The patient is 18–29, female; the palm and back of the hand are involved; this image was taken at an angle: 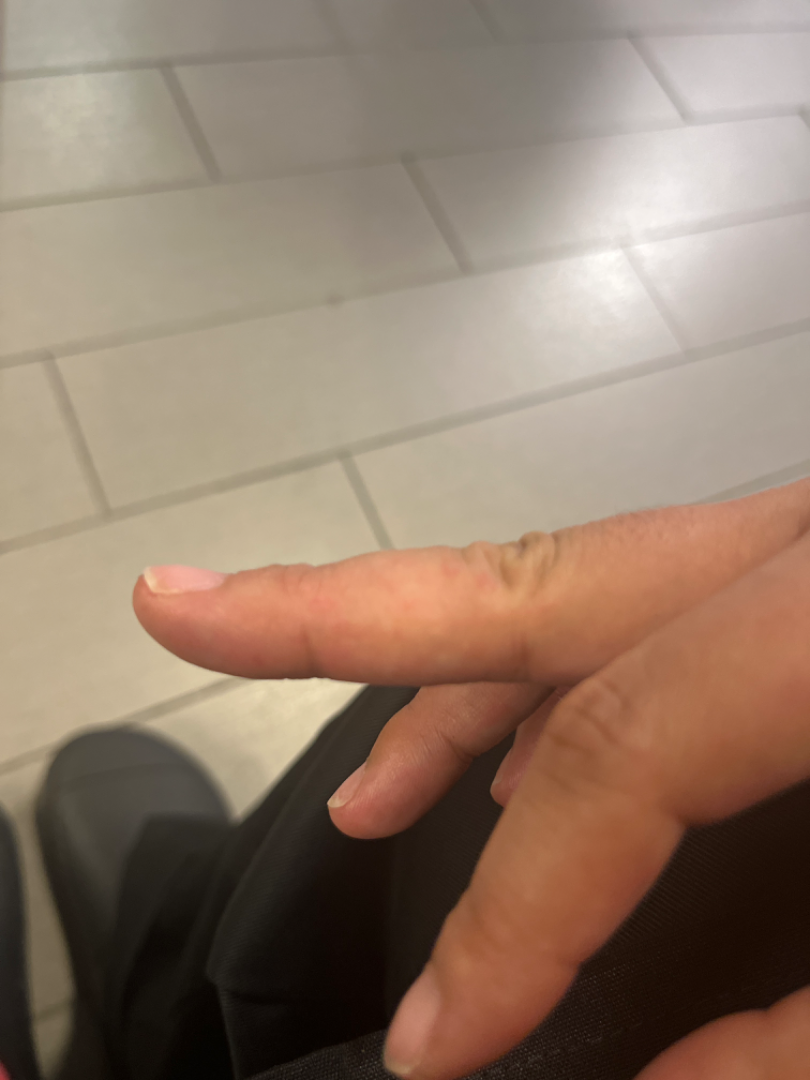The leading consideration is Eczema; possibly Allergic Contact Dermatitis.